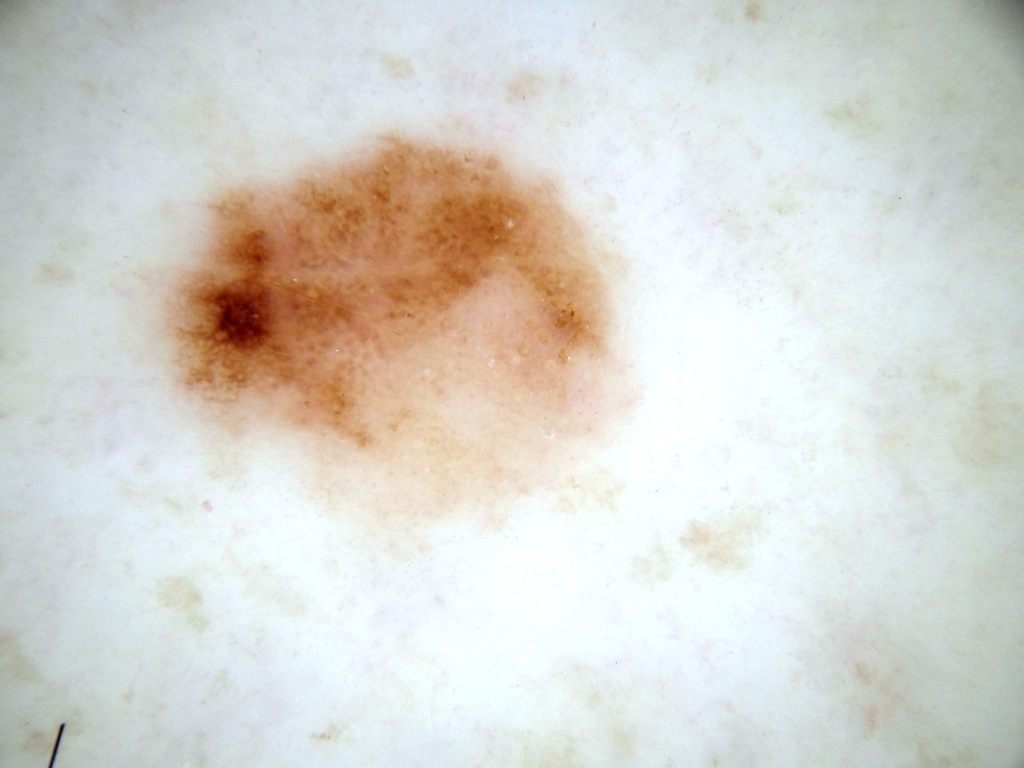  patient:
    sex: female
    age_approx: 50
  image:
    modality: dermoscopy
  lesion_location:
    bbox_xyxy:
      - 123
      - 114
      - 662
      - 581
  dermoscopic_features:
    present:
      - globules
      - negative network
      - pigment network
    absent:
      - streaks
      - milia-like cysts
  lesion_extent:
    approx_field_fraction_pct: 24
  diagnosis:
    name: melanocytic nevus
    malignancy: benign
    lineage: melanocytic
    provenance: clinical